The leg is involved · the condition has been present for less than one week · the photograph was taken at an angle.
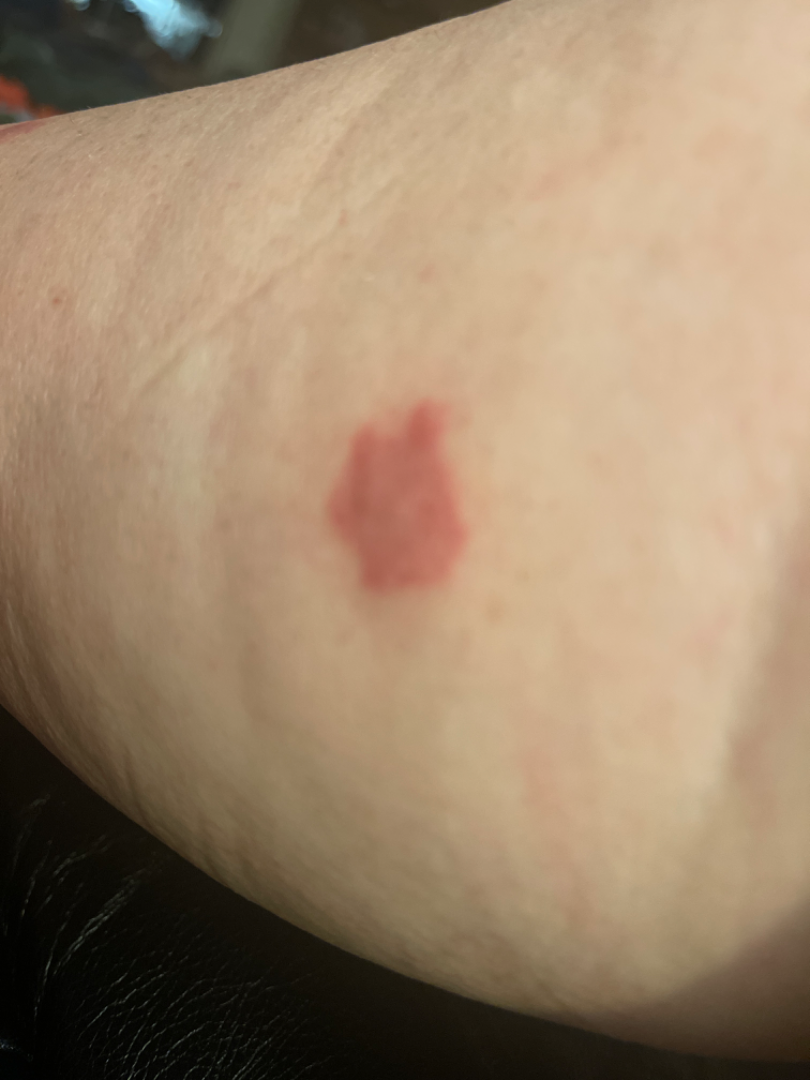The reviewing dermatologist's impression was: the leading consideration is Hemangioma; also raised was Insect Bite; also consider Tufted angioma of skin.